A dermoscopic image of a skin lesion.
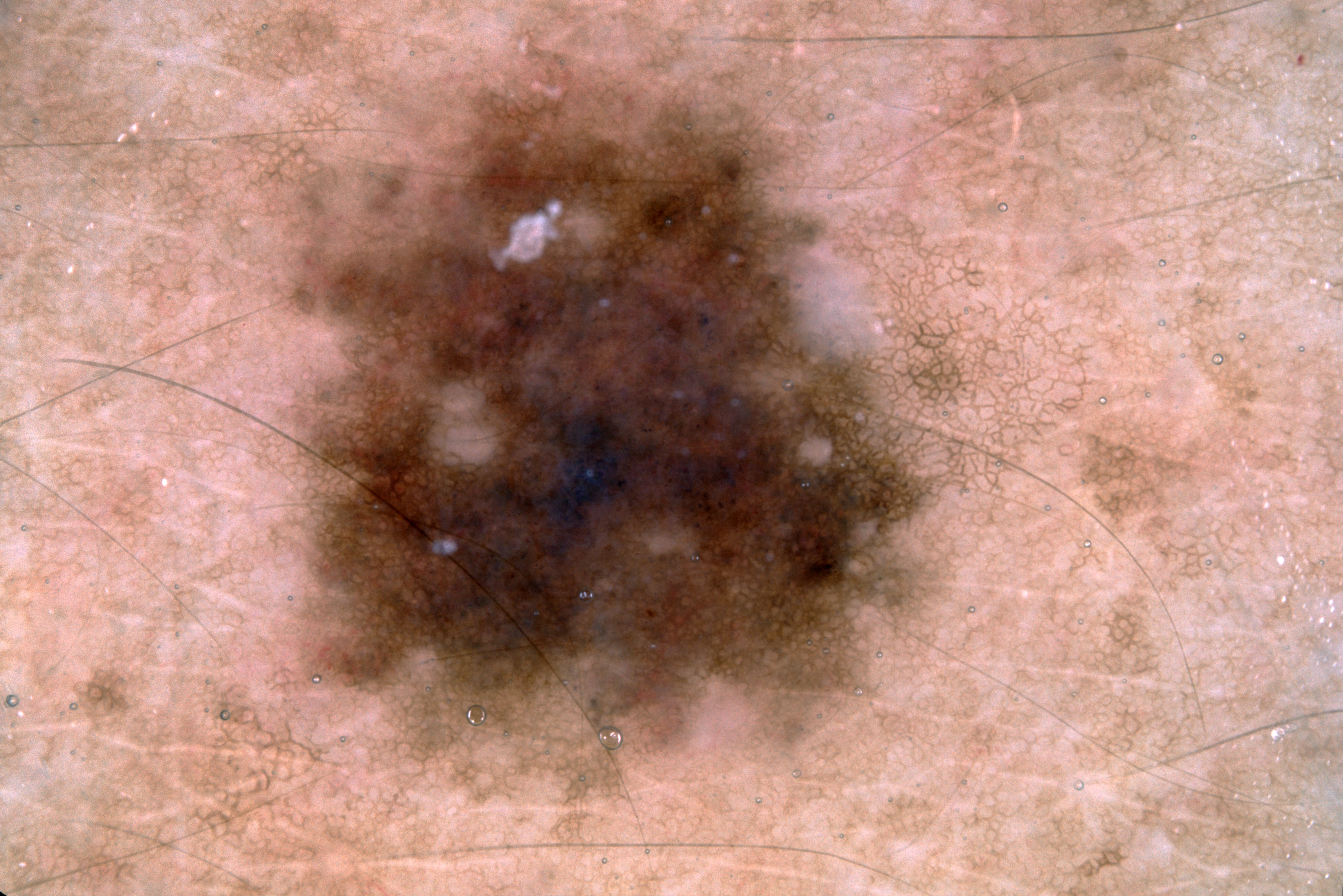Image and clinical context: Dermoscopic assessment notes pigment network; no negative network, milia-like cysts, or streaks. As (left, top, right, bottom), the lesion is bounded by [294,70,923,735]. A mid-sized lesion within the field. Impression: Expert review diagnosed this as a melanocytic nevus.